A dermoscopic image of a skin lesion.
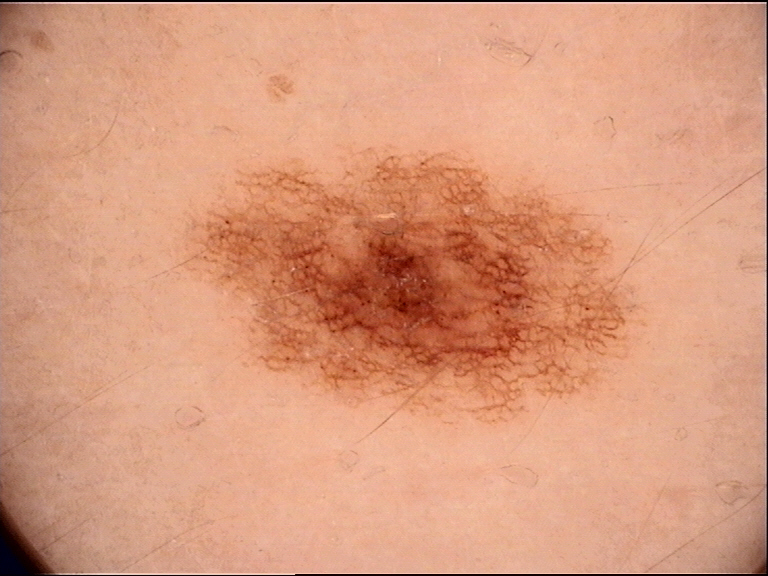diagnostic label: dysplastic junctional nevus (expert consensus).